Female contributor, age 40–49; the contributor reports itching; the contributor reports the lesion is flat; the contributor reports the condition has been present for more than one year; this is a close-up image; the leg is involved; skin tone: Fitzpatrick skin type III — 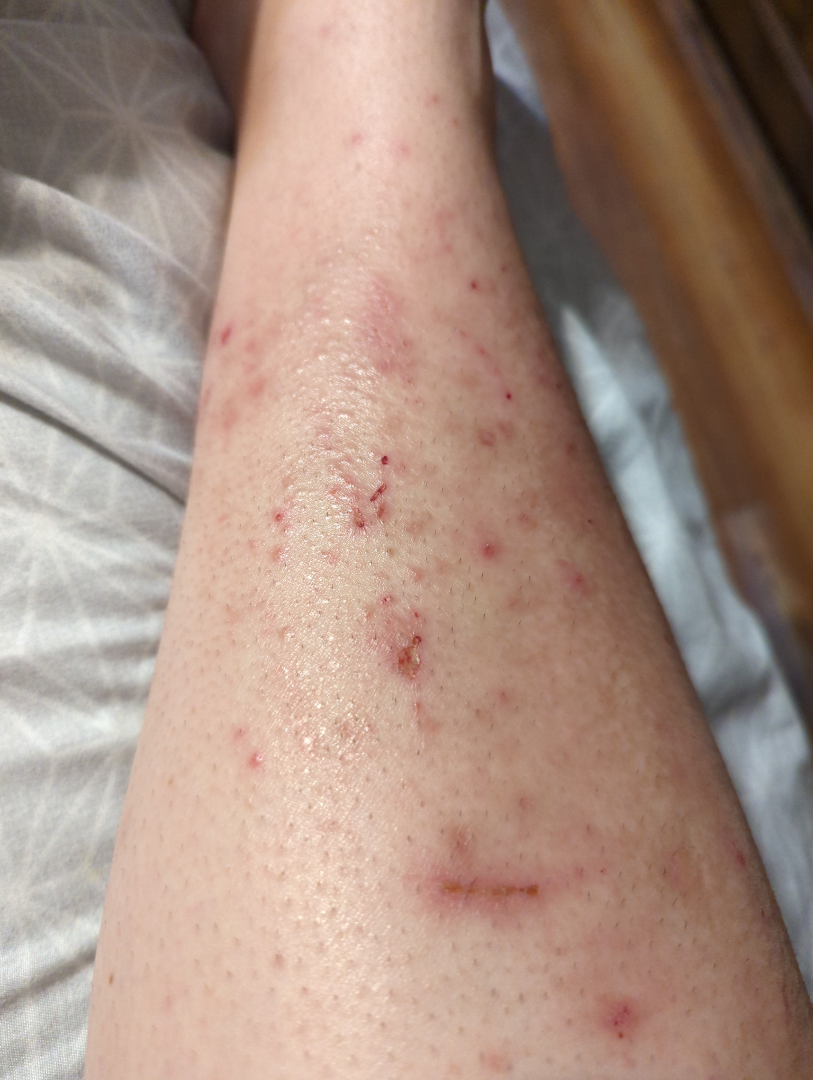Review: On remote review of the image, in keeping with Folliculitis.